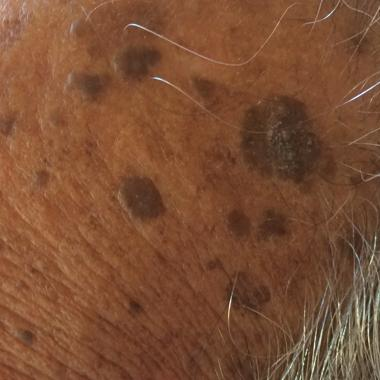The chart notes alcohol use. Measuring about 8 × 6 mm. The clinical impression was a seborrheic keratosis.